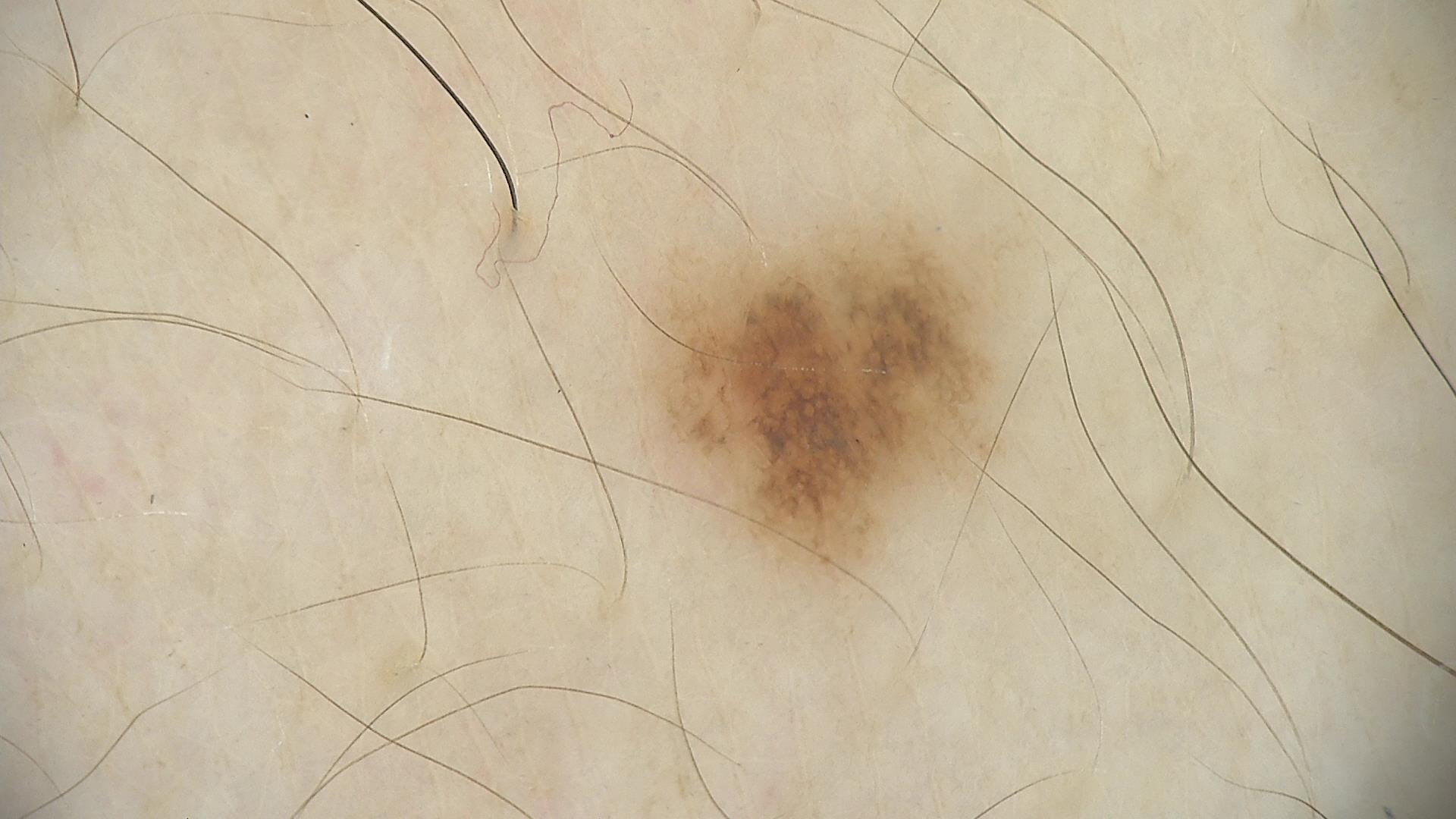Labeled as a dysplastic junctional nevus.